The lesion involves the arm · the photograph is a close-up of the affected area.
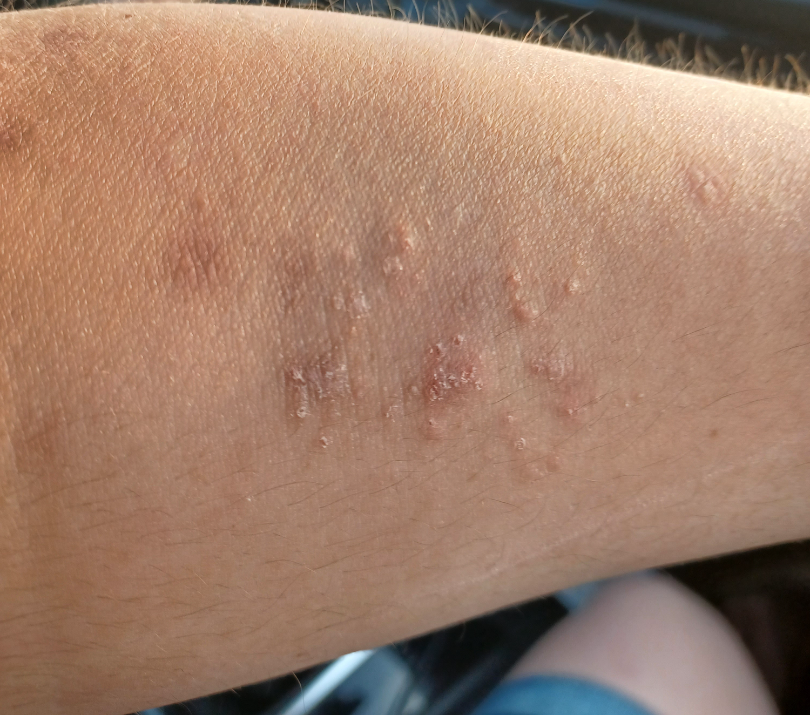differential:
  tied_lead:
    - Eczema
    - Allergic Contact Dermatitis
  considered:
    - Chronic dermatitis, NOS
  unlikely:
    - Herpes Zoster